The arm is involved. An image taken at an angle: 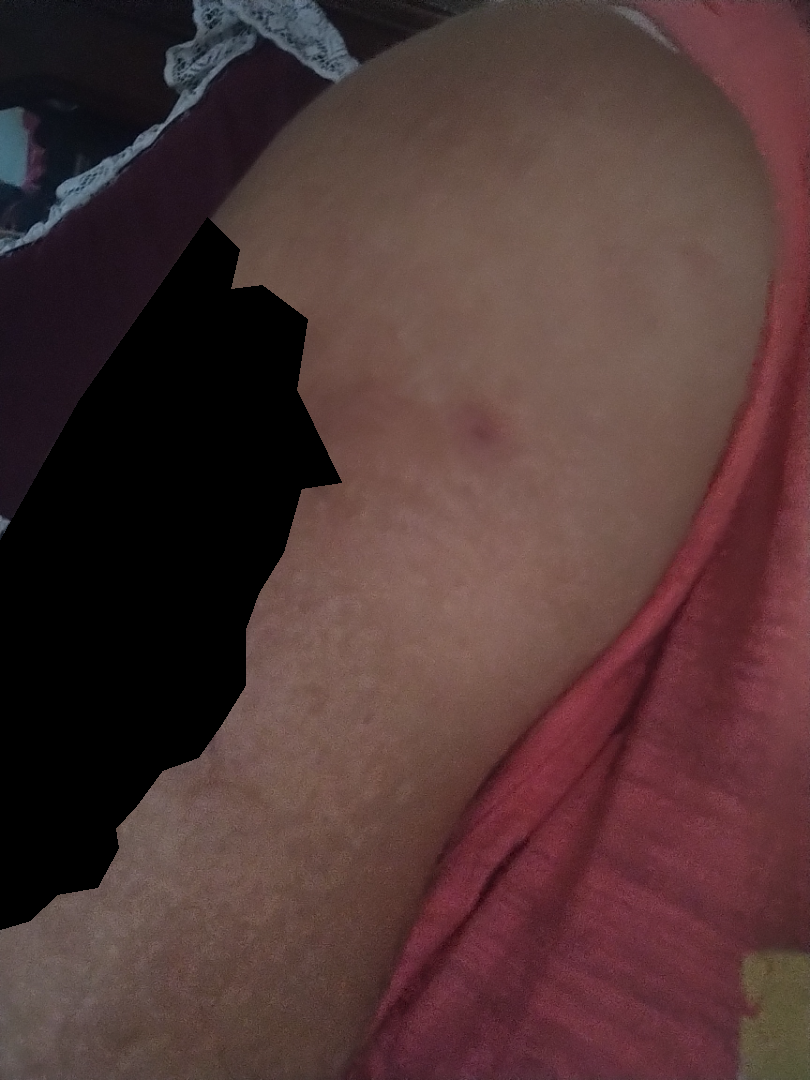Most consistent with Folliculitis; an alternative is Eczema.